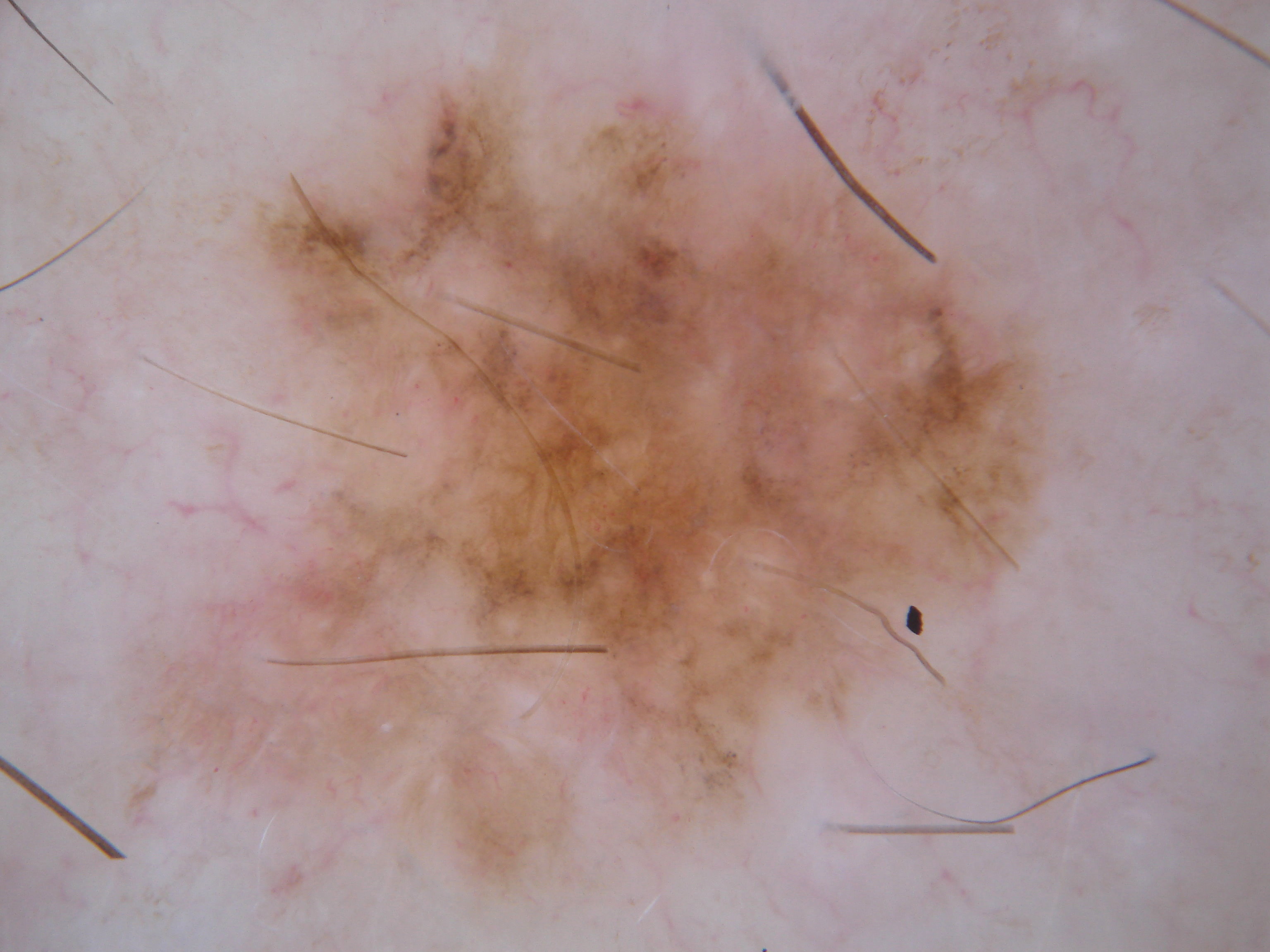image — dermoscopy of a skin lesion
dermoscopic findings — globules; absent: milia-like cysts, pigment network, streaks, and negative network
bounding box — x1=107, y1=10, x2=1113, y2=943
lesion extent — ~54% of the field
diagnosis — a melanoma